A dermoscopic close-up of a skin lesion.
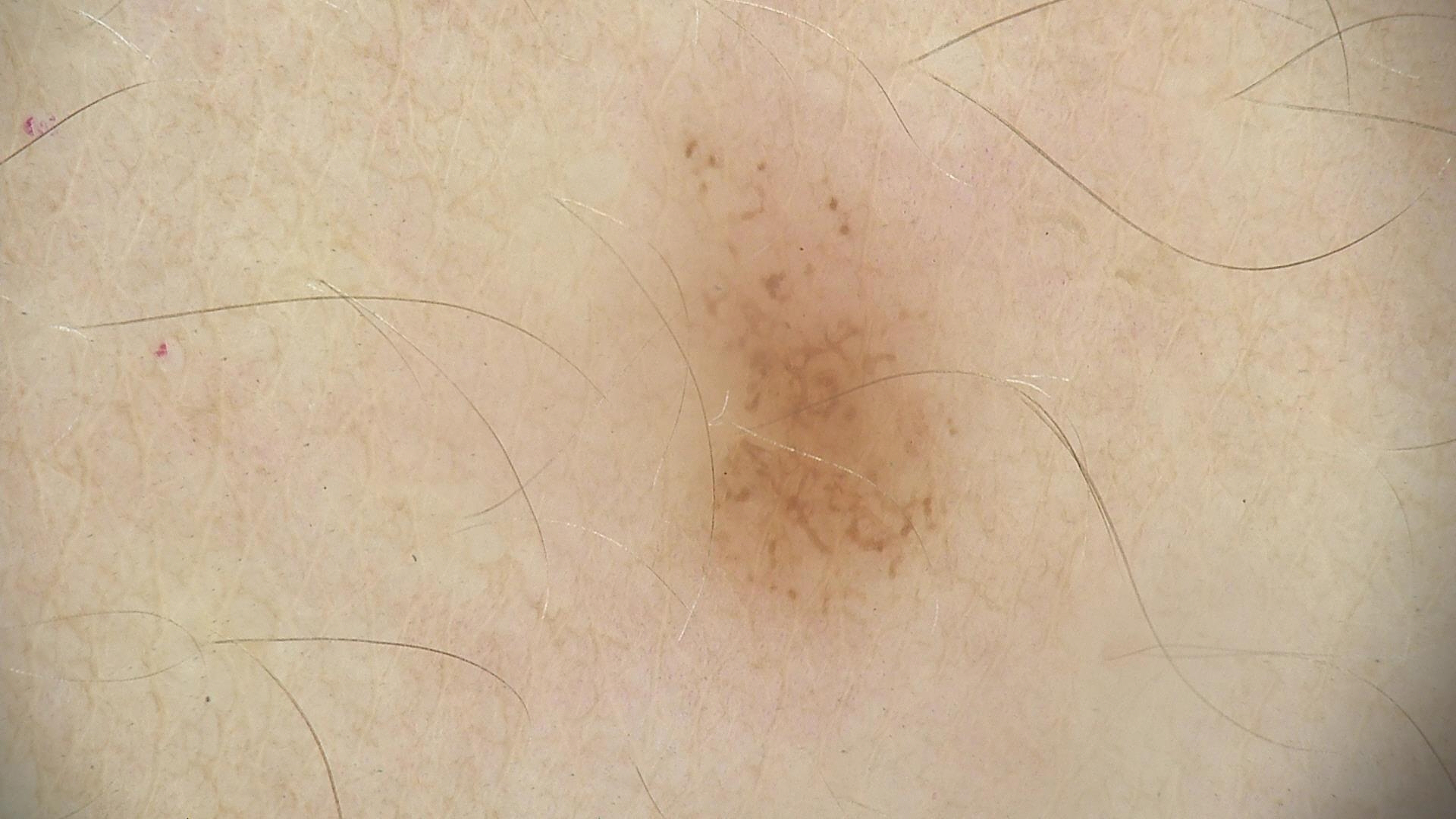<lesion>
<diagnosis>
<name>dysplastic junctional nevus</name>
<code>jd</code>
<malignancy>benign</malignancy>
<super_class>melanocytic</super_class>
<confirmation>expert consensus</confirmation>
</diagnosis>
</lesion>